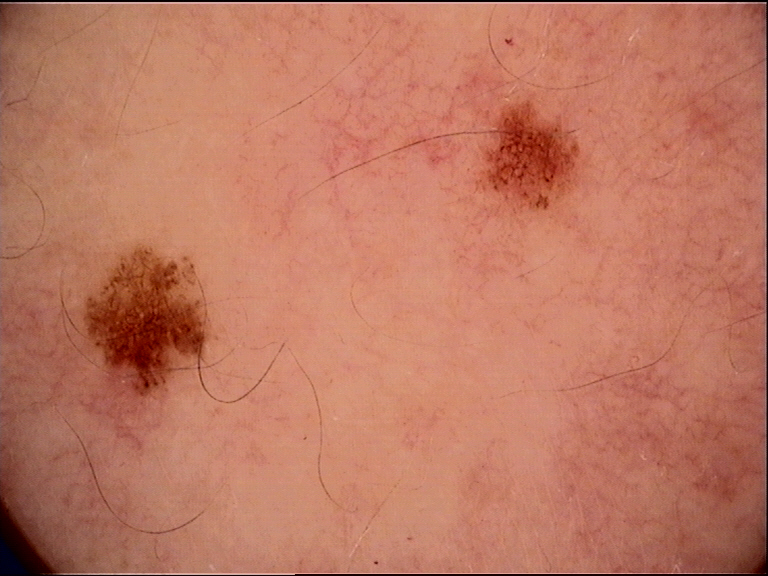label = dysplastic junctional nevus (expert consensus).